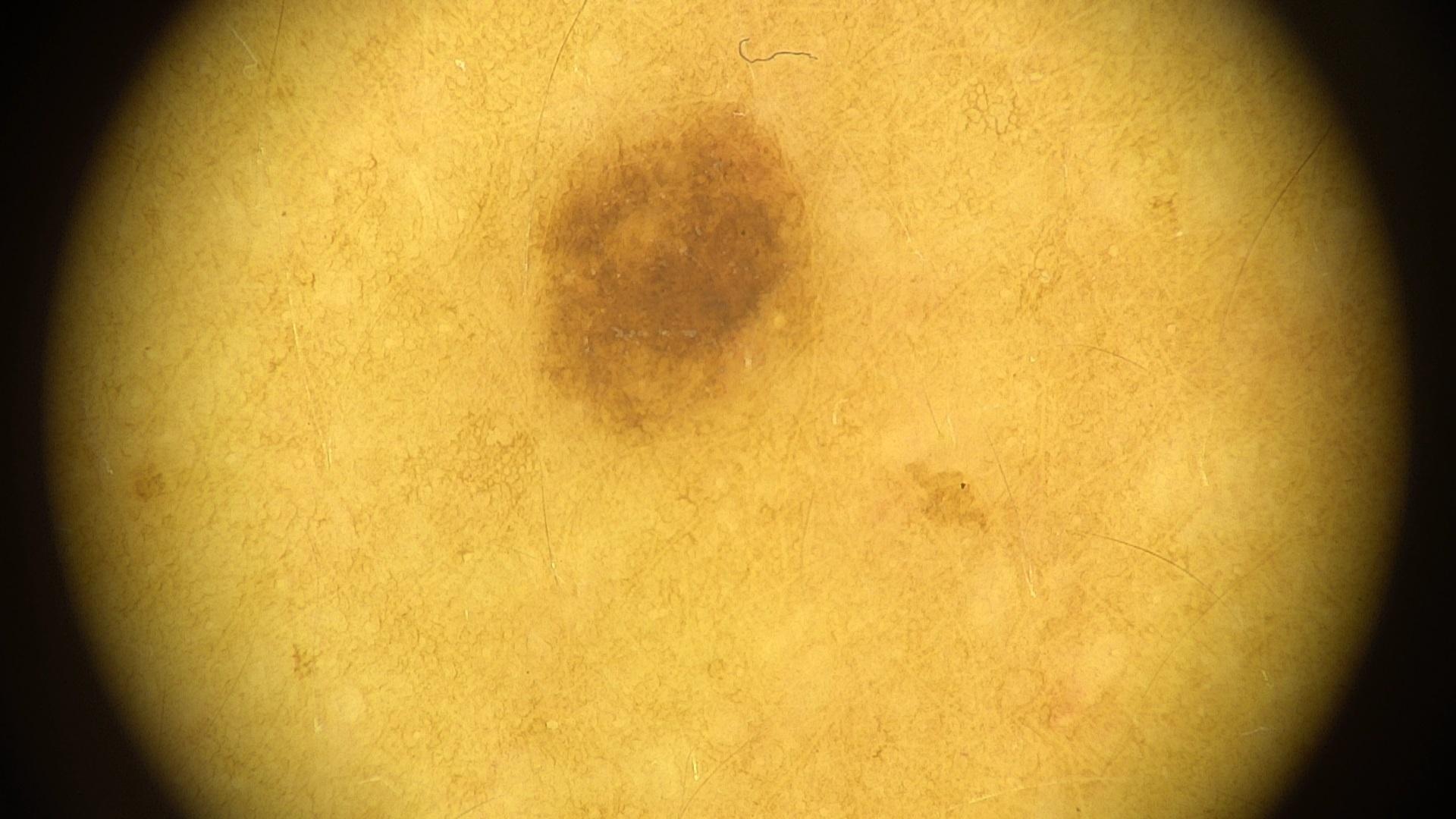The lesion is on the posterior trunk. Clinically diagnosed as a melanocytic lesion — a nevus.